Referred for assessment of suspected melanocytic nevus. The patient says their skin reddens with sun exposure. Dermoscopy of a skin lesion. A female patient age 59. The patient describes having a moderate number of moles:
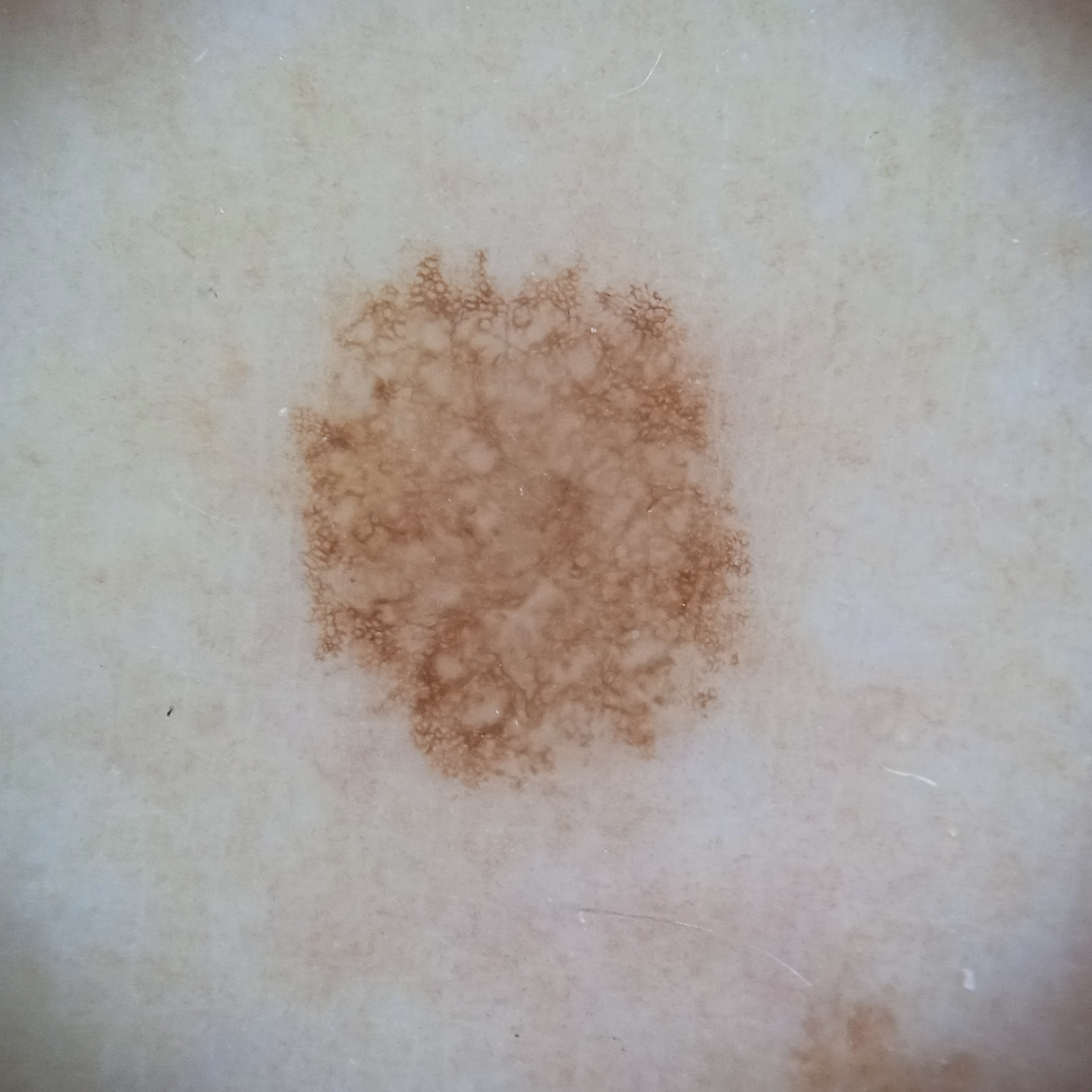The lesion is located on an arm. Histopathologically confirmed as an atypical (dysplastic) nevus, following excision.